The lesion is described as raised or bumpy · an image taken at a distance · the contributor notes the condition has been present for one to four weeks · the patient considered this skin that appeared healthy to them · the contributor notes itching · the leg and arm are involved.
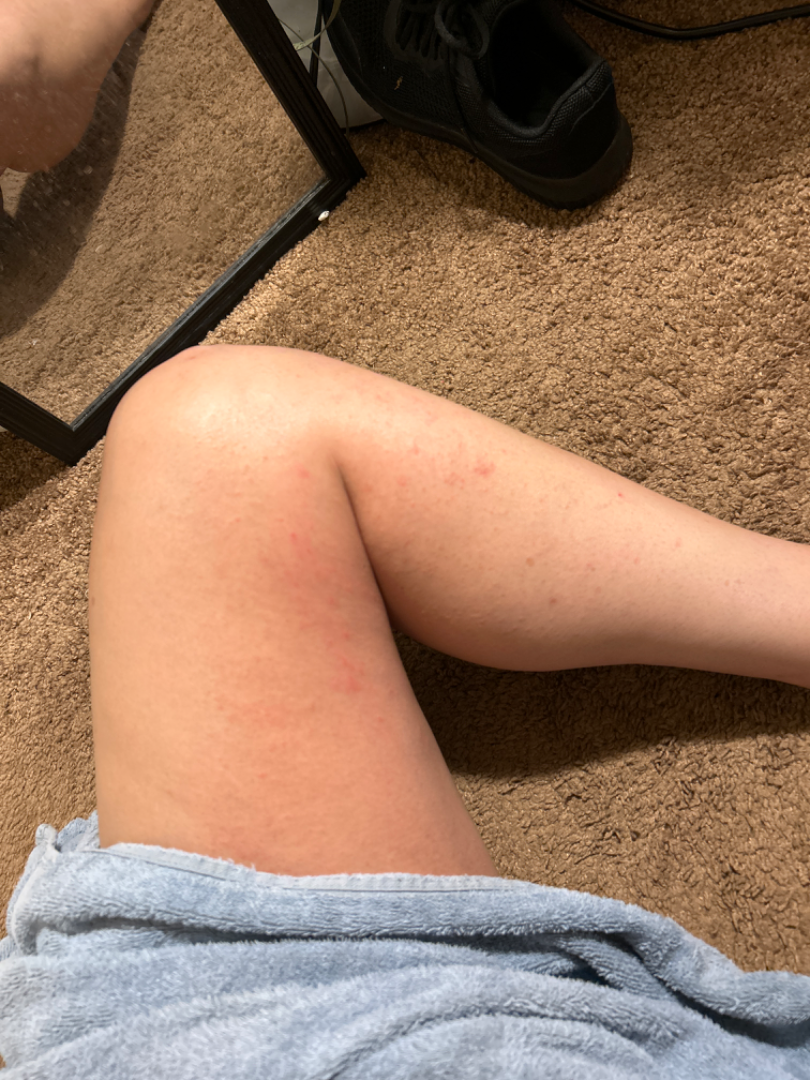The case was difficult to assess from the available photograph.